A dermoscopic close-up of a skin lesion.
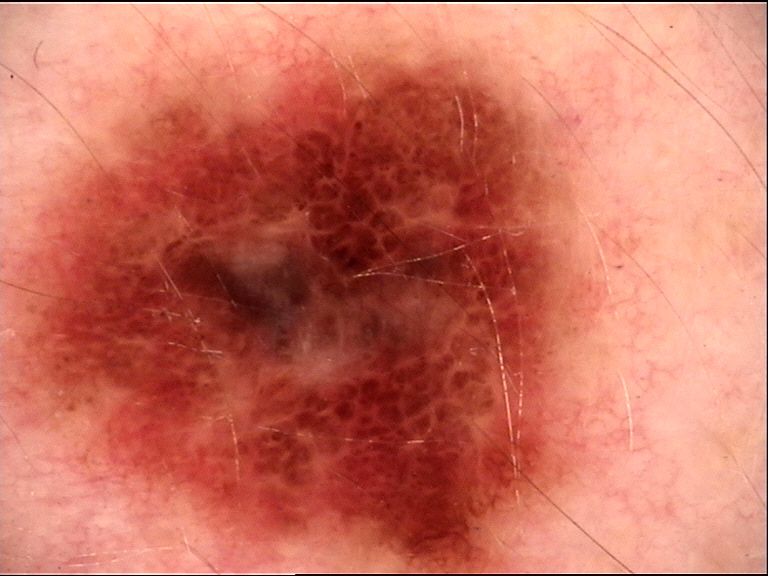Pathology:
The biopsy diagnosis was a melanoma.